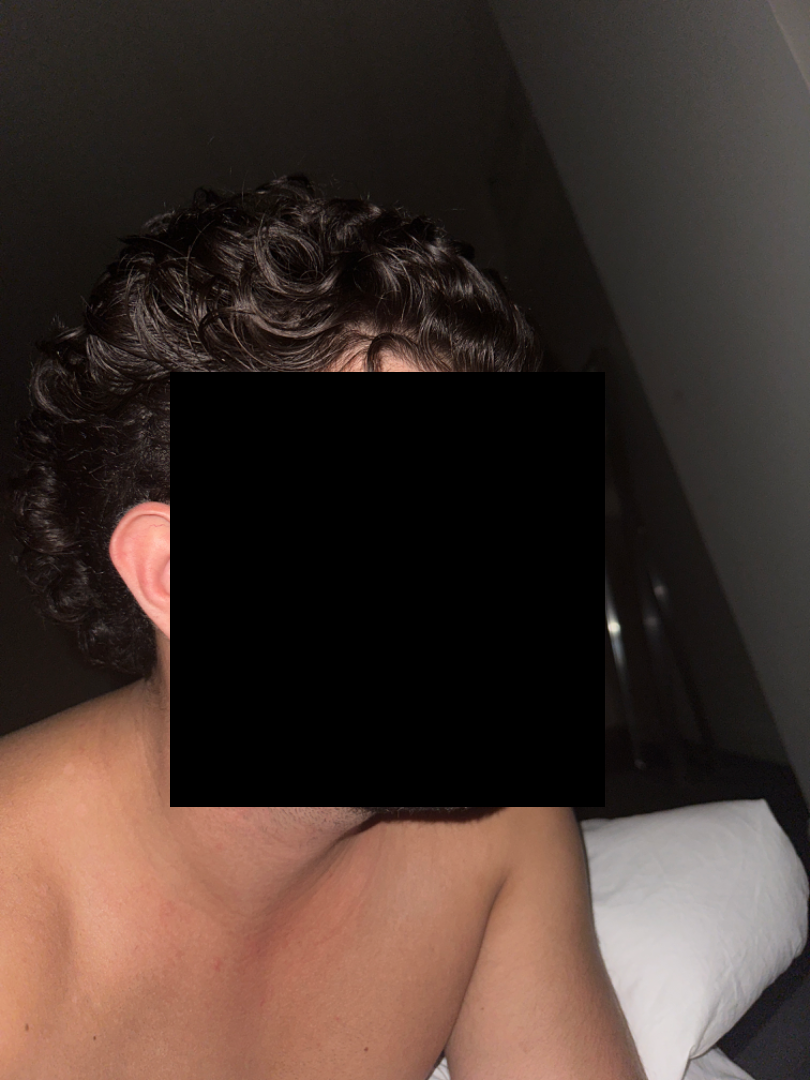{"differential": {"leading": ["Acne"], "considered": ["Rosacea"]}}